The photograph is a close-up of the affected area. The lesion involves the front of the torso and back of the torso:
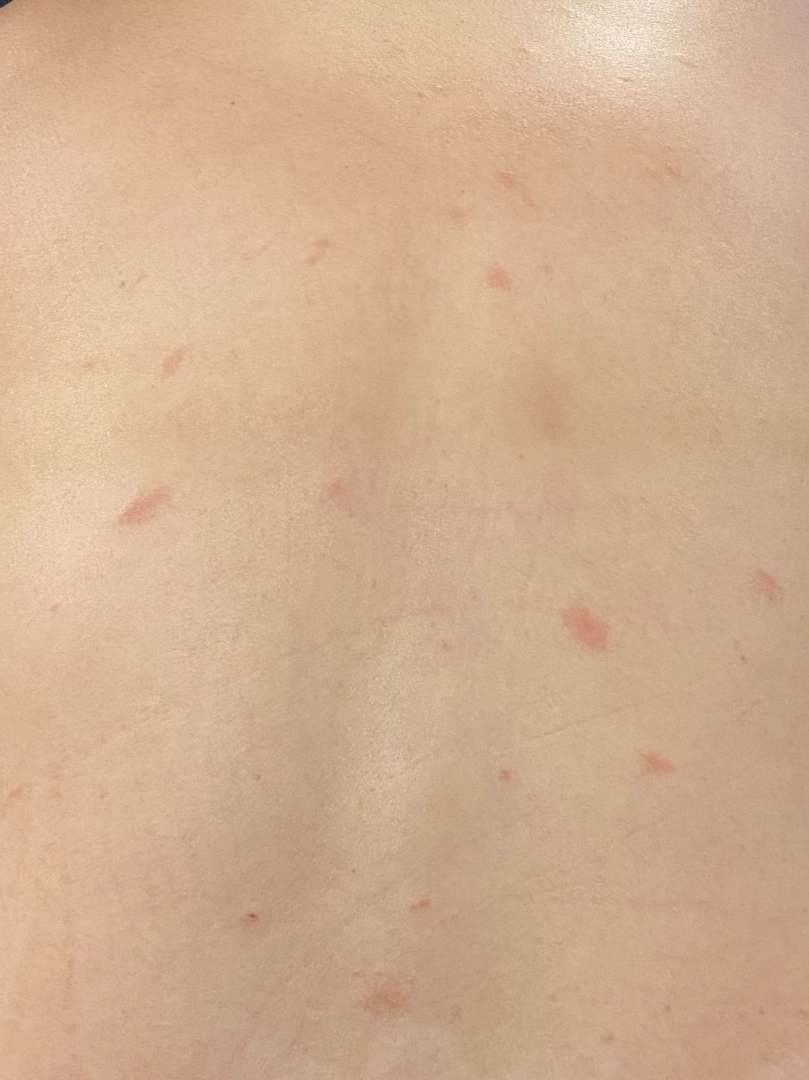Clinical context: Self-categorized by the patient as a rash. Fitzpatrick skin type II; lay reviewers estimated Monk Skin Tone 2 or 3. Present for less than one week. The contributor notes the lesion is flat and raised or bumpy. Assessment: Most likely Pityriasis rosea.